A dermoscopic close-up of a skin lesion: 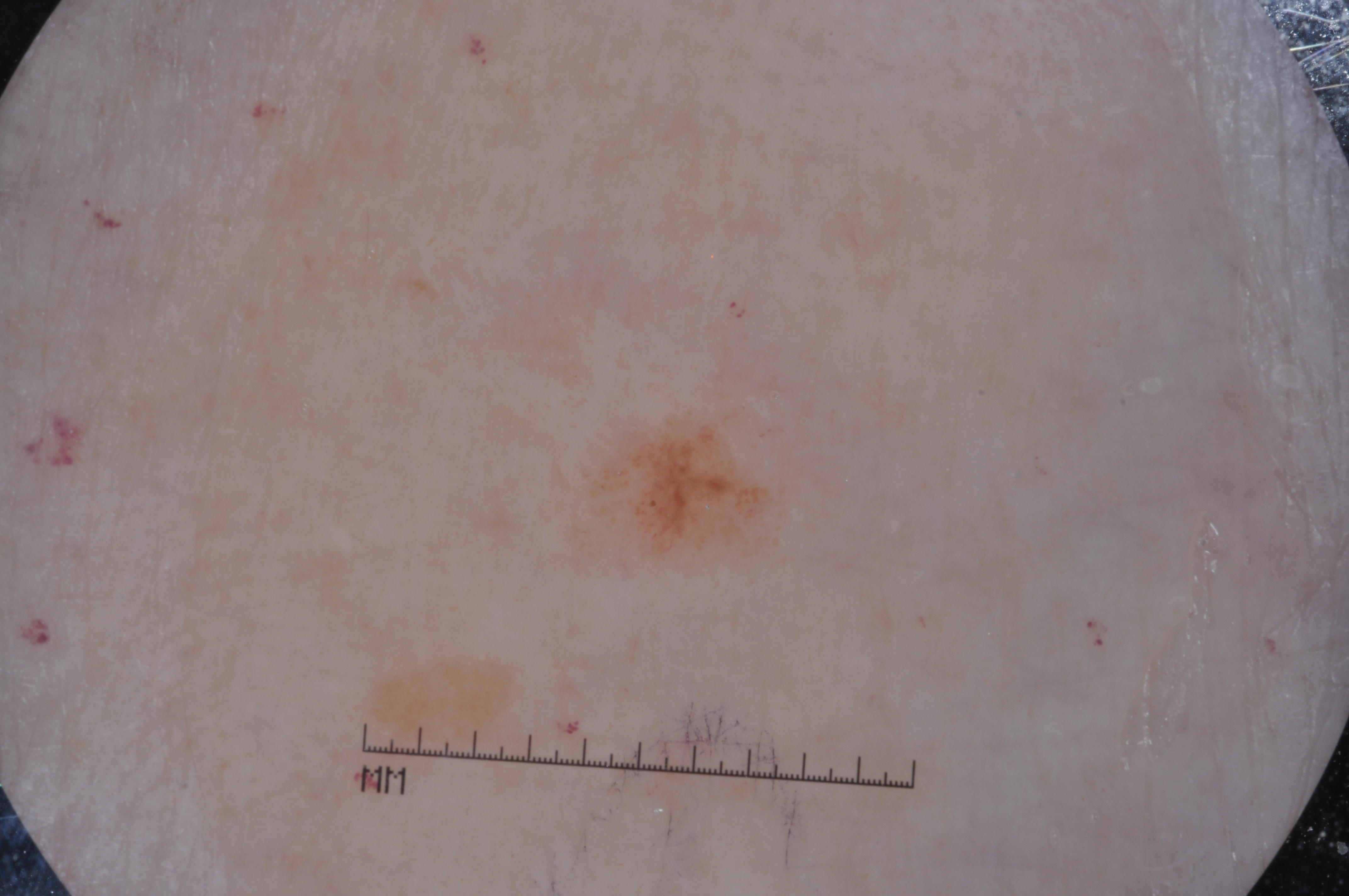A small lesion occupying a minor part of the field. Dermoscopic examination shows milia-like cysts and negative network; no pigment network or streaks. The visible lesion spans [622,434,769,553]. Diagnosed as a melanocytic nevus, a benign lesion.